An image taken at an angle:
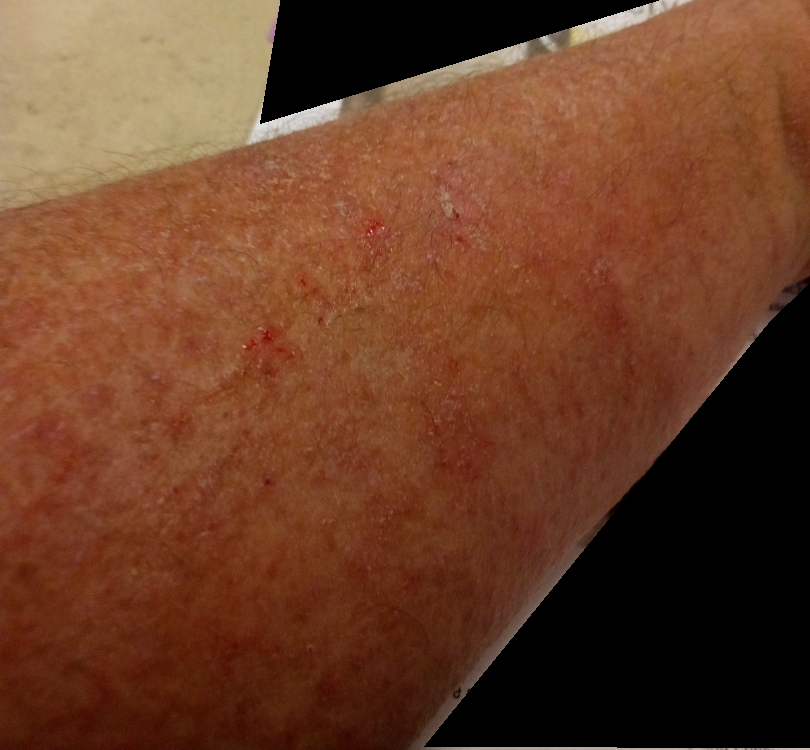Impression: The image was not sufficient for the reviewer to characterize the skin condition.